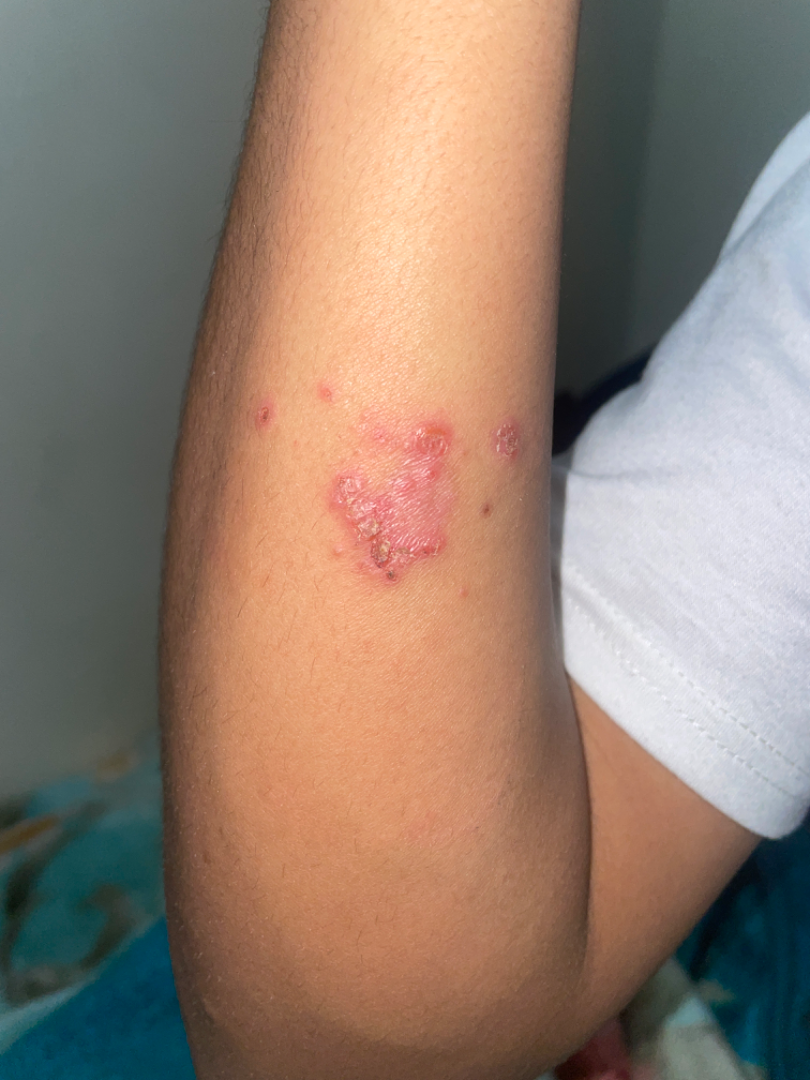{"skin_tone": {"fitzpatrick": "IV"}, "symptoms": ["pain", "itching", "enlargement", "burning"], "systemic_symptoms": "none reported", "shot_type": "close-up", "duration": "one to four weeks", "body_site": "arm", "patient": "male, age 18–29", "texture": ["flat", "rough or flaky"], "differential": "Impetigo"}